A skin lesion imaged with a dermatoscope.
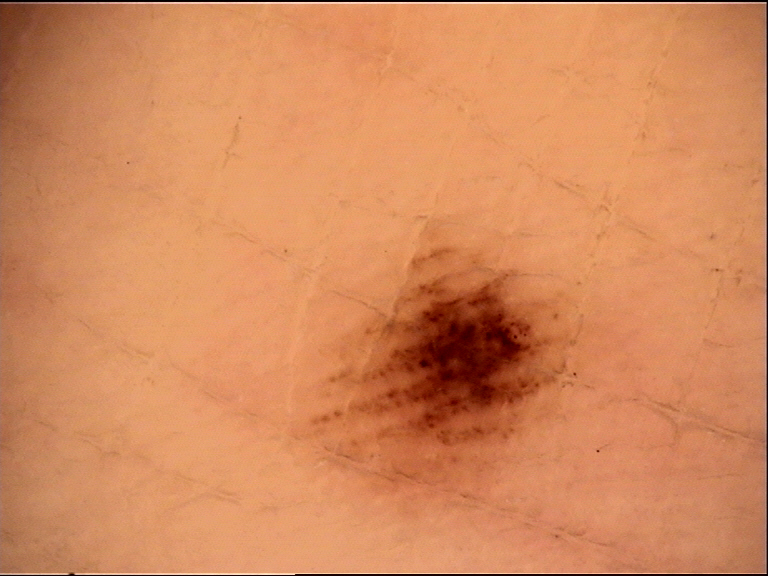Consistent with an acral dysplastic junctional nevus.